A dermatoscopic image of a skin lesion:
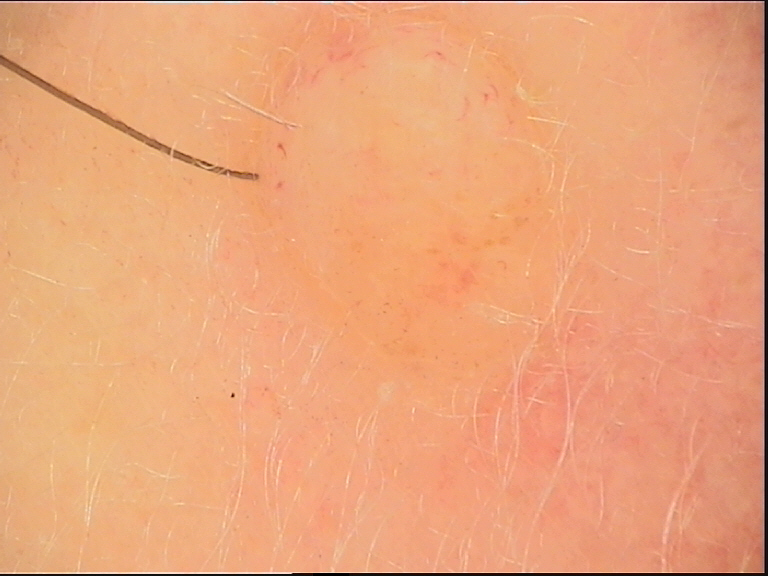The architecture is that of a banal lesion. Classified as a dermal nevus.